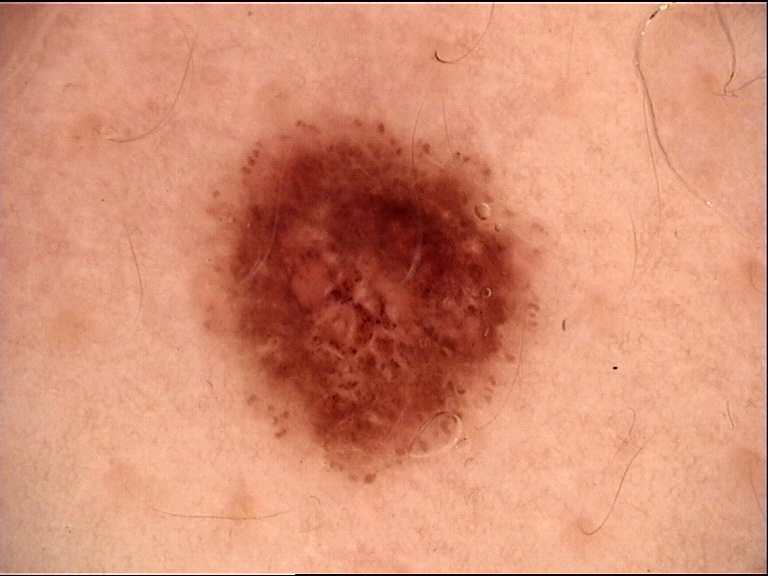A dermoscopic close-up of a skin lesion.
Consistent with a dysplastic junctional nevus.